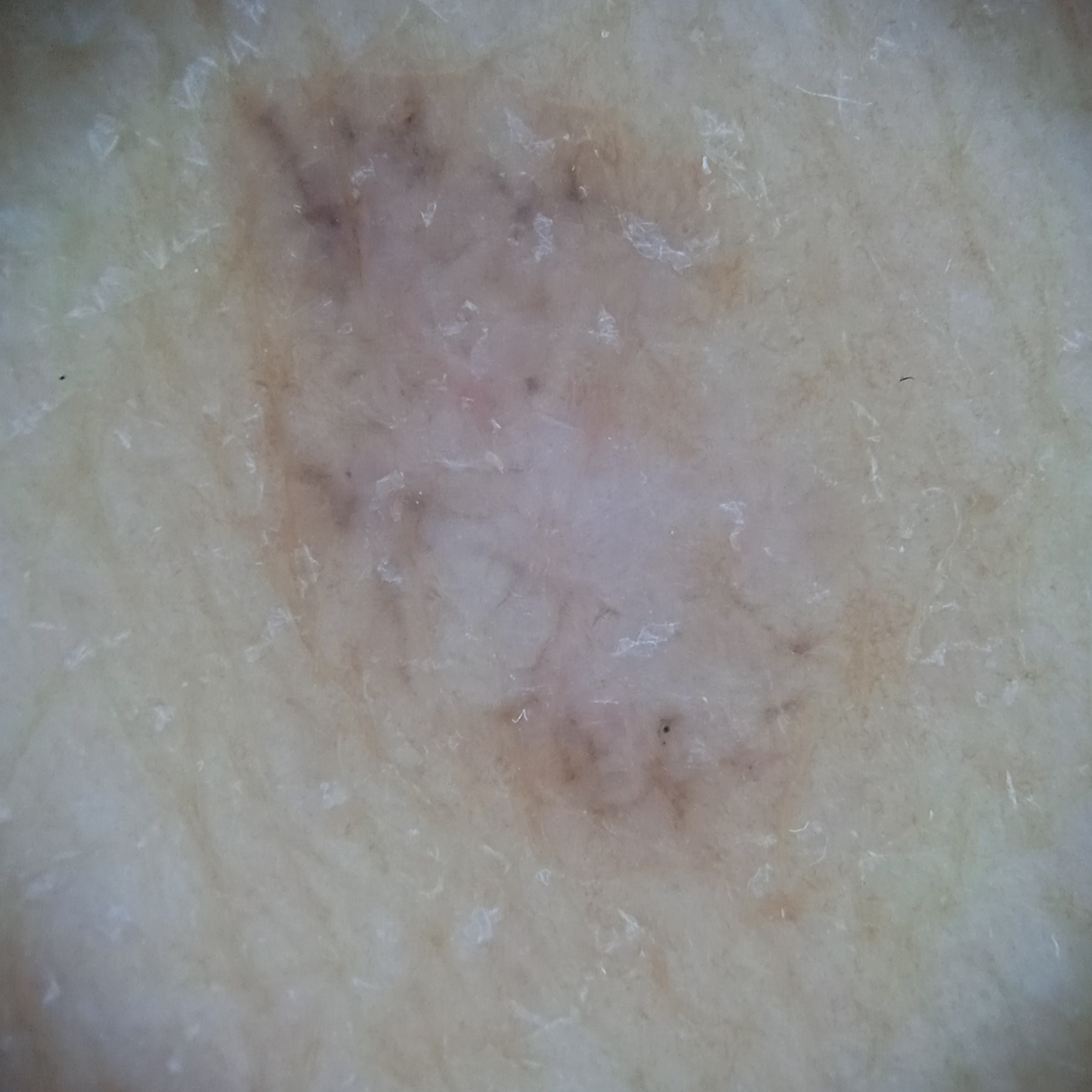Q: What kind of image is this?
A: dermatoscopic image
Q: How does the patient's skin react to sun?
A: skin tans without first burning
Q: What is the patient's nevus burden?
A: few melanocytic nevi overall
Q: Why was this imaged?
A: research study (no referral diagnosis)
Q: What is the anatomic site?
A: the back
Q: How large is the lesion?
A: 10.4 mm
Q: What was the diagnosis?
A: basal cell carcinoma (dermatologist consensus)